A female patient age 71. Imaged for a research study, with no referral diagnosis recorded. A dermoscopy image of a skin lesion.
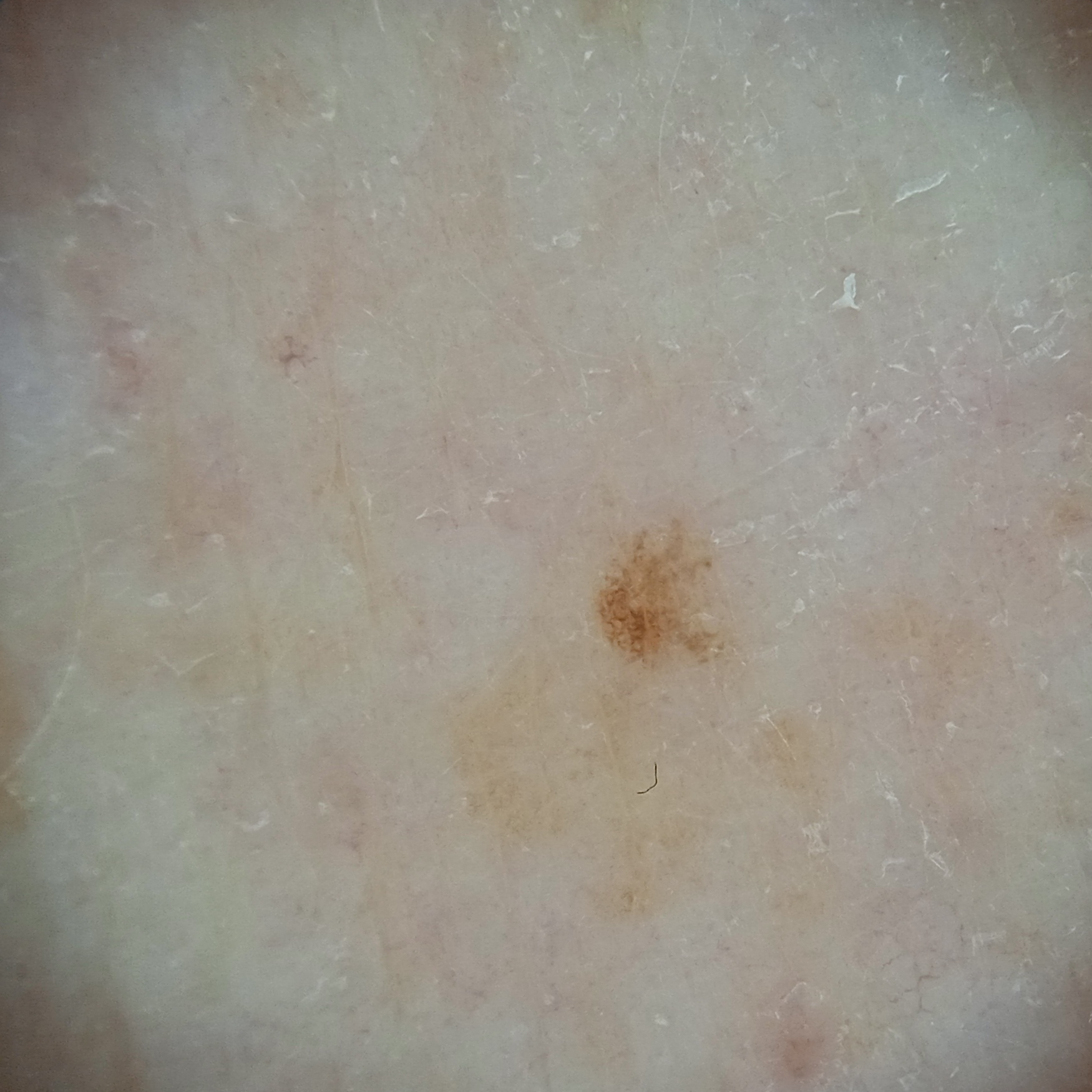The lesion involves an arm. The lesion measures approximately 1.7 mm. The dermatologists' assessment was a melanocytic nevus.